Dermoscopy of a skin lesion: 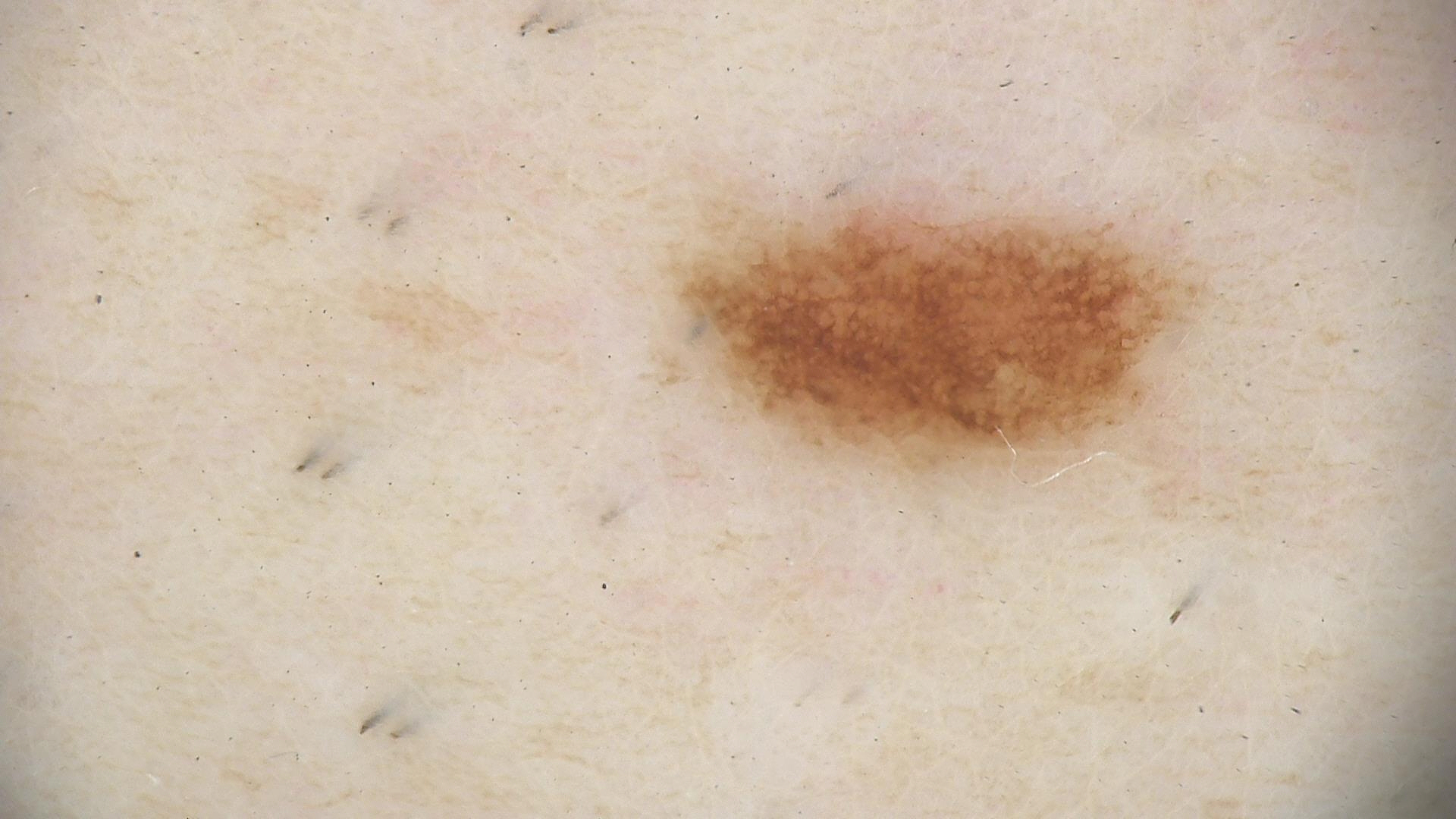Diagnosed as a junctional nevus.